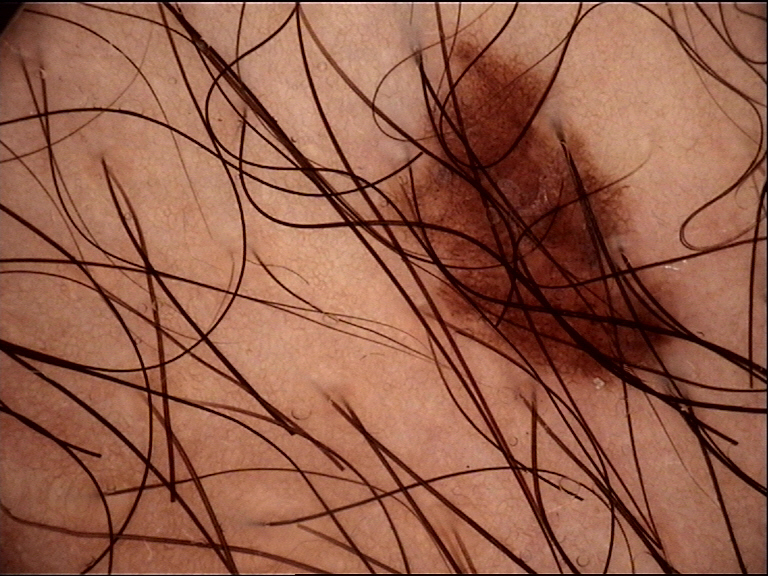A dermoscopic image of a skin lesion. Classified as a junctional nevus.